A male patient, aged around 15. A dermoscopic view of a skin lesion:
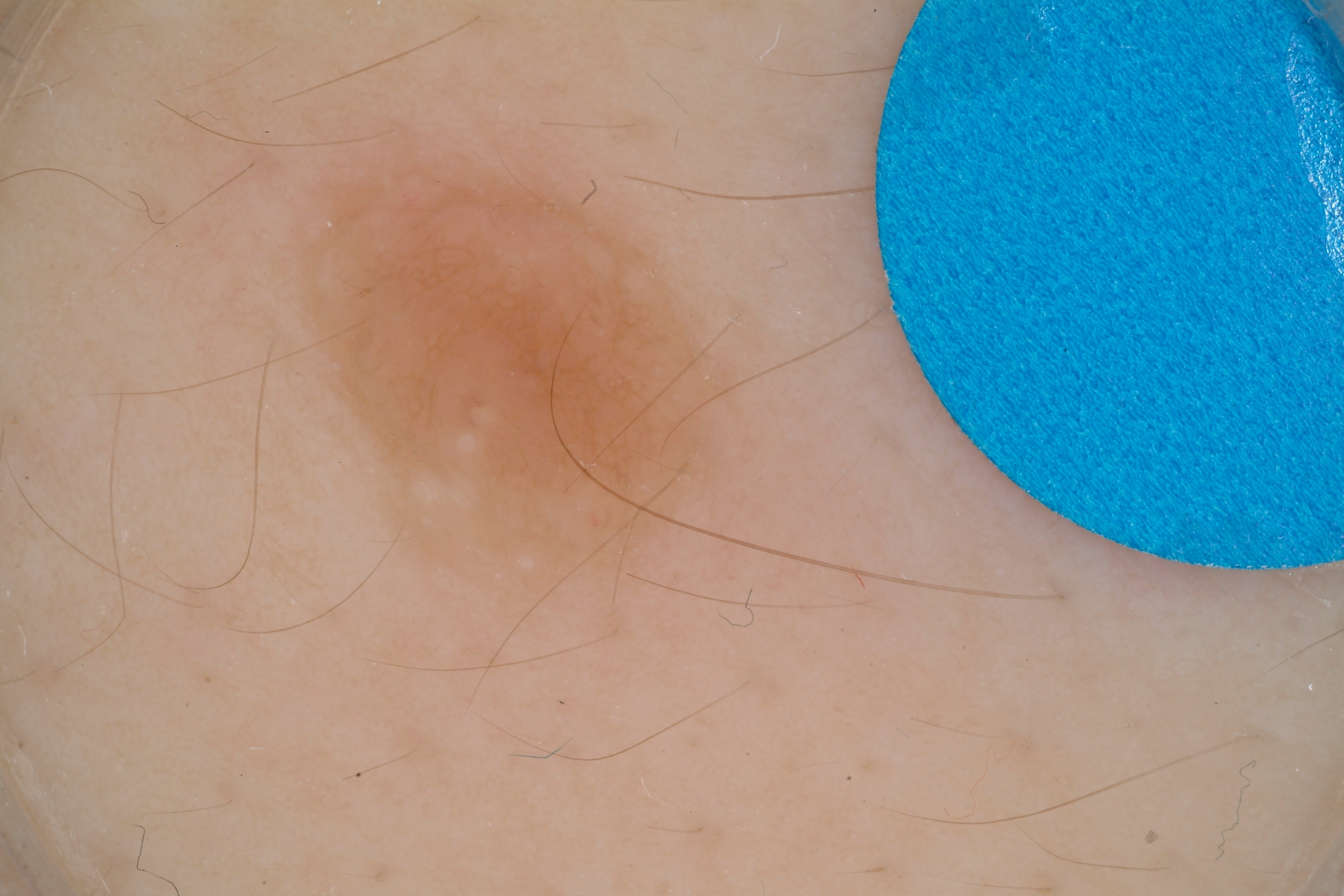  lesion_location:
    bbox_xyxy:
      - 275
      - 149
      - 729
      - 599
  dermoscopic_features:
    present:
      - milia-like cysts
      - pigment network
    absent:
      - negative network
      - globules
      - streaks
  diagnosis:
    name: melanocytic nevus
    malignancy: benign
    lineage: melanocytic
    provenance: clinical